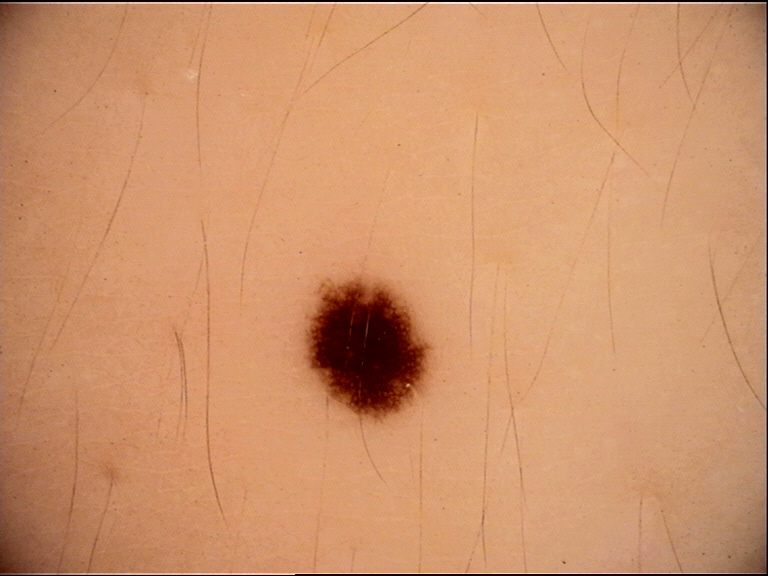{"diagnosis": {"name": "dysplastic junctional nevus", "code": "jd", "malignancy": "benign", "super_class": "melanocytic", "confirmation": "expert consensus"}}